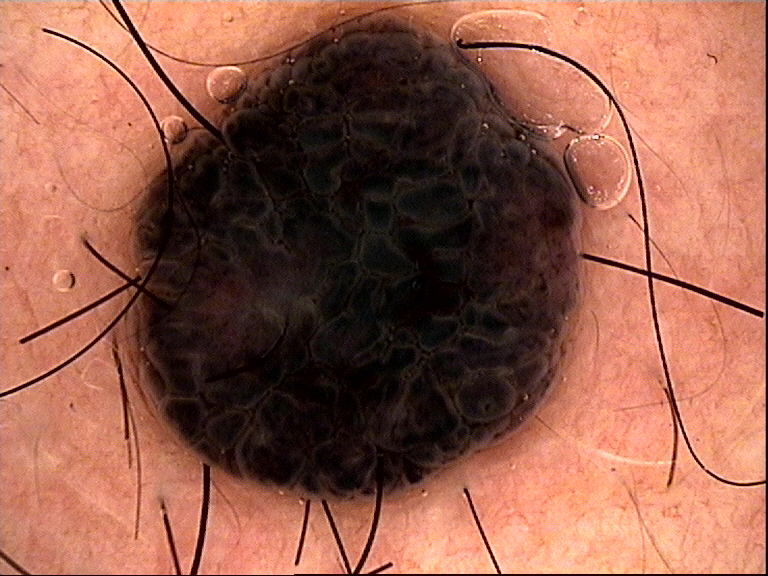imaging = dermoscopy; category = banal; assessment = compound nevus (expert consensus).